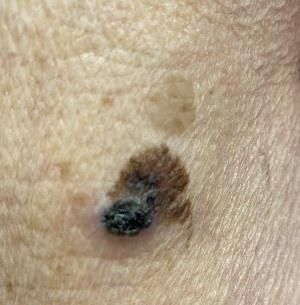Image and clinical context:
Fitzpatrick phototype II. A female subject aged 73 to 77. The lesion involves an upper extremity.
Conclusion:
Histopathology confirmed a melanoma.